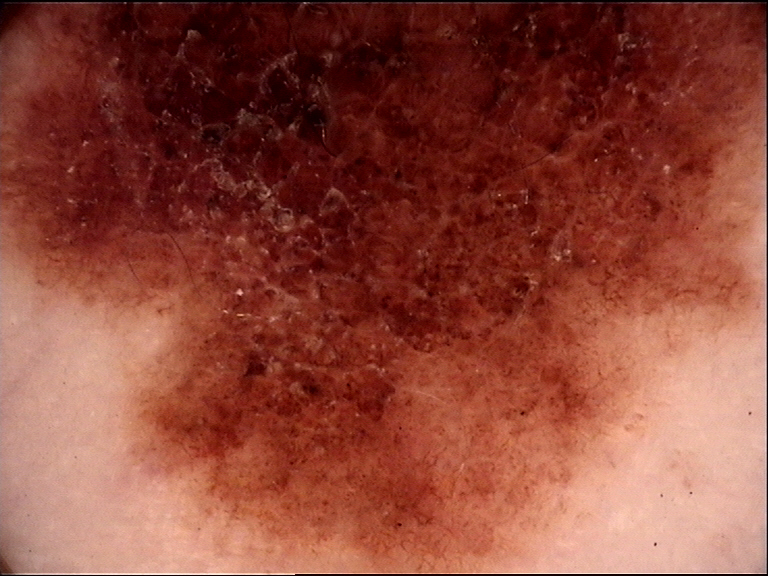A dermoscopic close-up of a skin lesion. Classified as a dysplastic compound nevus.